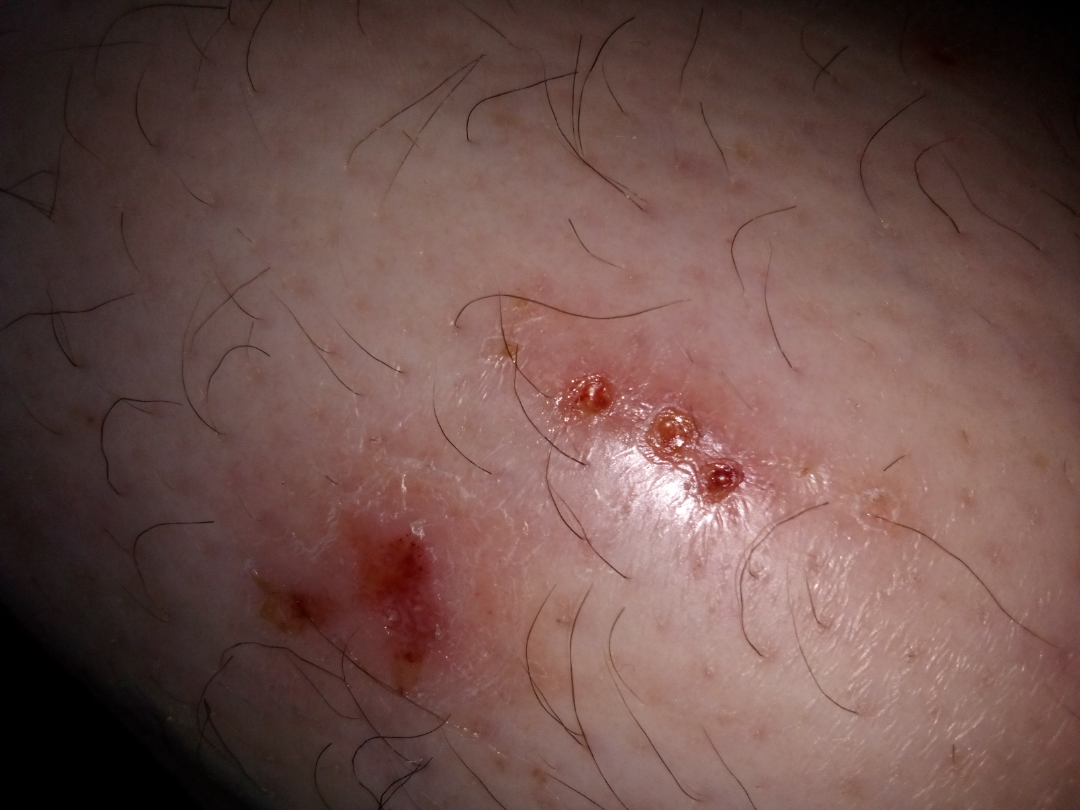<report>
<assessment>ungradable on photographic review</assessment>
<duration>more than one year</duration>
<patient_category>a growth or mole</patient_category>
<symptoms>enlargement, bothersome appearance, darkening, itching, pain, bleeding, burning</symptoms>
<shot_type>at an angle</shot_type>
<body_site>leg</body_site>
</report>